Female subject, age 60–69 · an image taken at an angle · the affected area is the front of the torso and back of the torso: 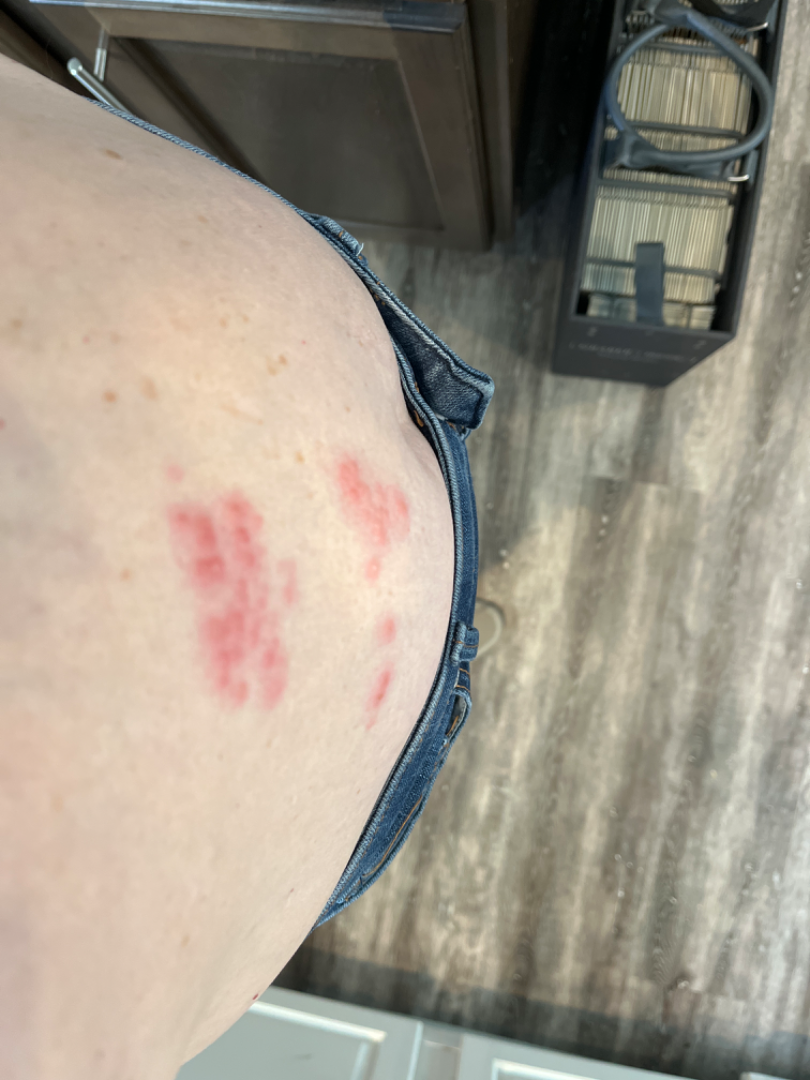Findings:
– patient-reported symptoms — bothersome appearance
– symptom duration — less than one week
– dermatologist impression — Herpes Zoster (0.78); Allergic Contact Dermatitis (0.11); Herpes Simplex (0.11)